Dermoscopy of a skin lesion — 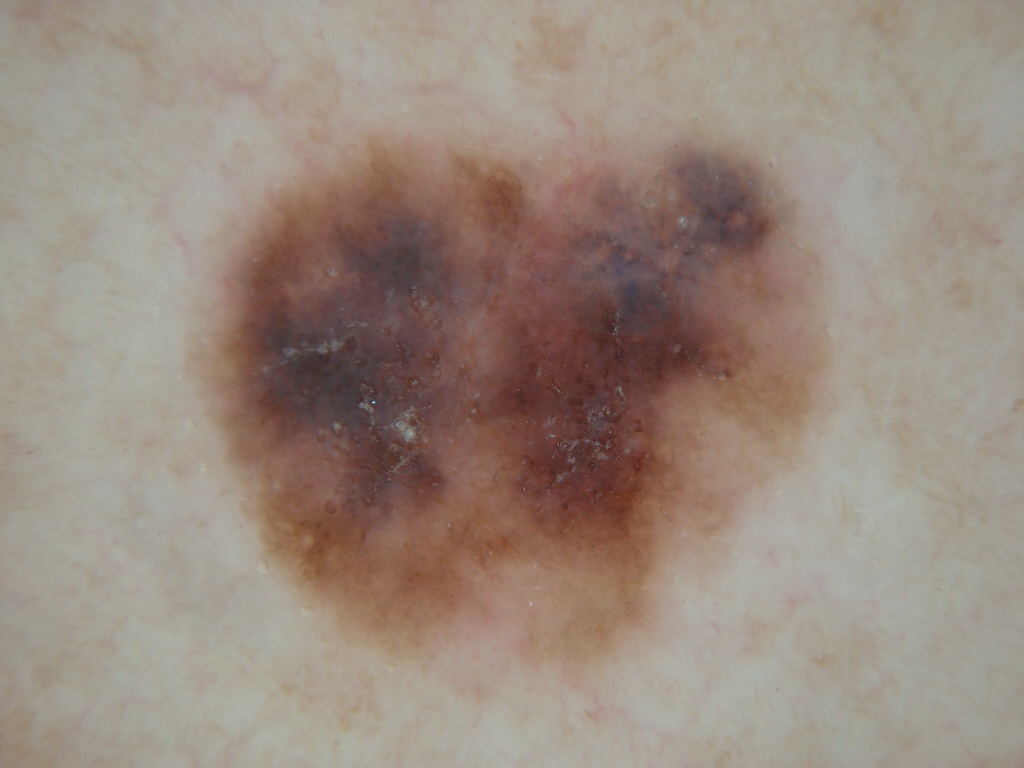The lesion is located at left=186, top=106, right=832, bottom=687. The lesion takes up a large portion of the image. Dermoscopic review identifies no pigment network, milia-like cysts, negative network, streaks, or globules. Confirmed on histopathology as a melanoma.